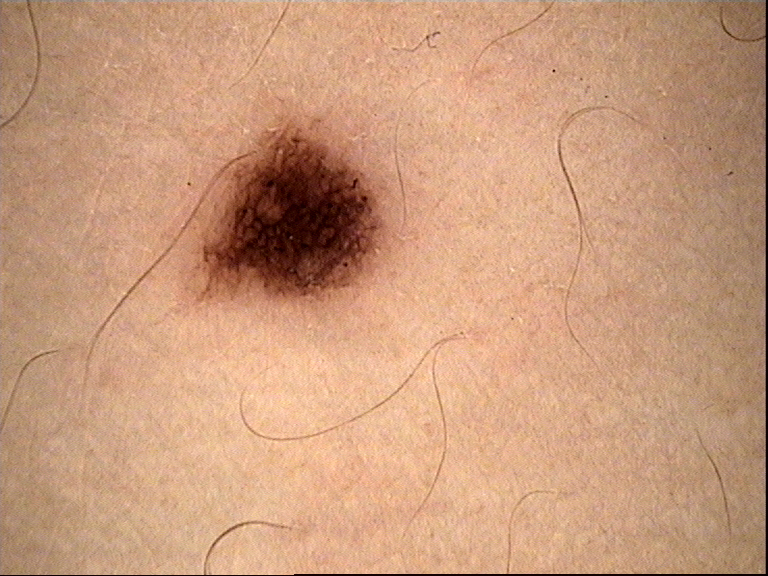| key | value |
|---|---|
| modality | dermatoscopy |
| diagnosis | dysplastic junctional nevus (expert consensus) |